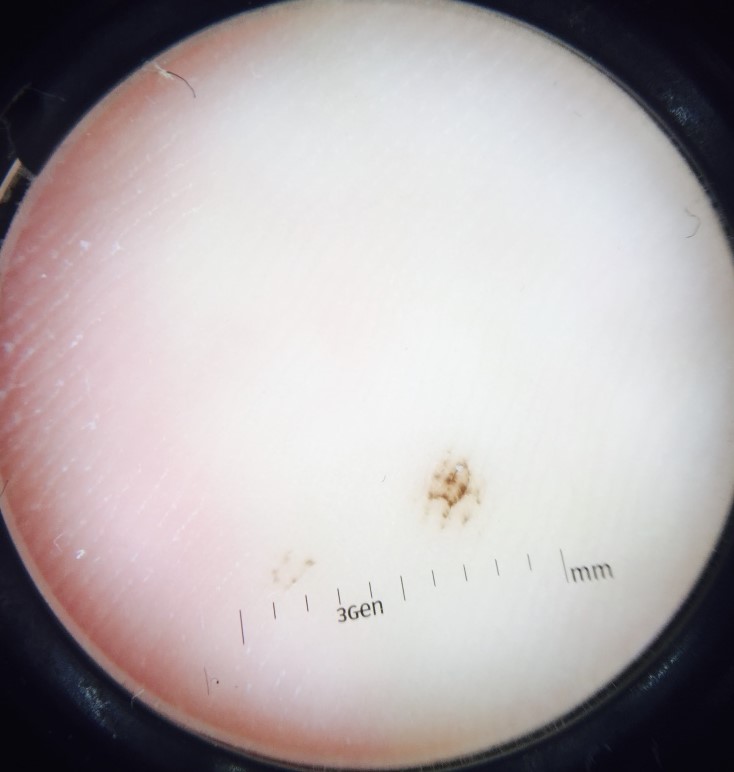A dermoscopic image of a skin lesion. The diagnostic label was a benign lesion — an acral dysplastic junctional nevus.